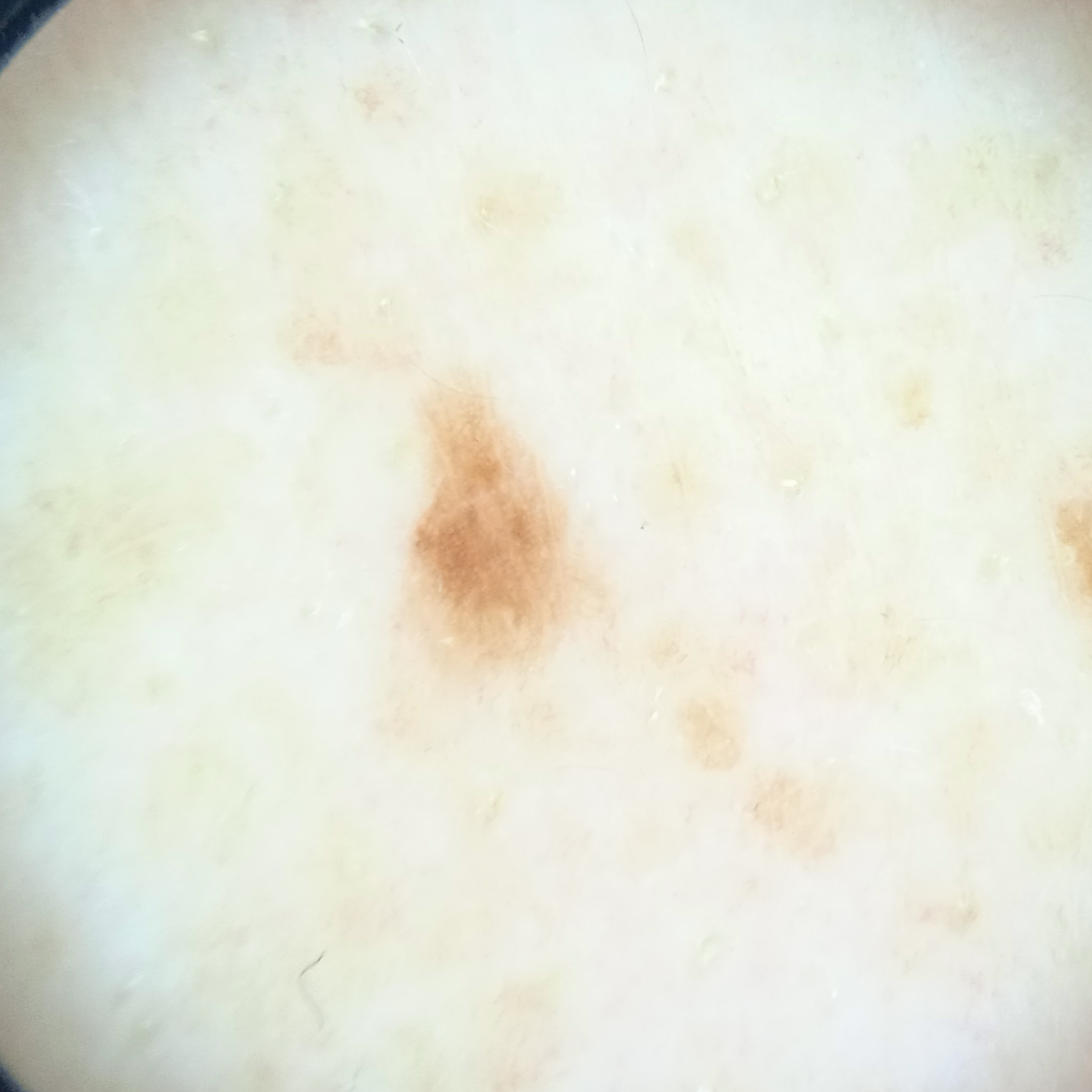Q: Why was this imaged?
A: clinical suspicion of melanocytic nevus
Q: What is the imaging modality?
A: dermatoscopic image
Q: What are the relevant risk factors?
A: a personal history of skin cancer, a personal history of cancer, a family history of skin cancer
Q: How does the patient's skin react to sun?
A: skin tans without first burning
Q: Patient demographics?
A: male, 58 years of age
Q: What is the patient's nevus burden?
A: numerous melanocytic nevi
Q: What is the anatomic site?
A: the back
Q: Lesion size?
A: 3.2 mm
Q: What was the diagnosis?
A: melanocytic nevus (dermatologist consensus)